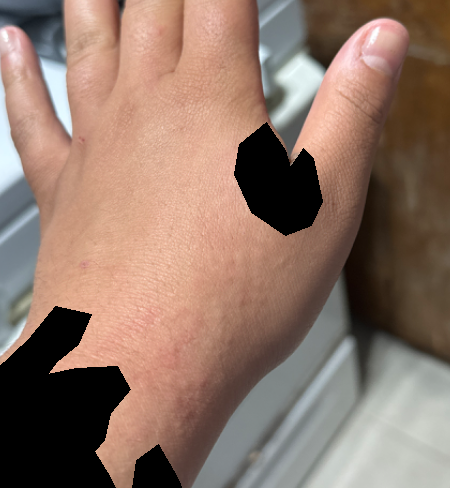{"patient_category": "a rash", "shot_type": "at a distance", "skin_tone": {"fitzpatrick": "IV", "monk_skin_tone": [2, 4]}, "body_site": ["back of the hand", "arm"], "patient": "female, age 18–29", "symptoms": "itching", "texture": "raised or bumpy", "differential": {"tied_lead": ["Contact dermatitis", "Allergic Contact Dermatitis"], "unlikely": ["Urticaria", "Hypersensitivity"]}}